Dermoscopy of a skin lesion: 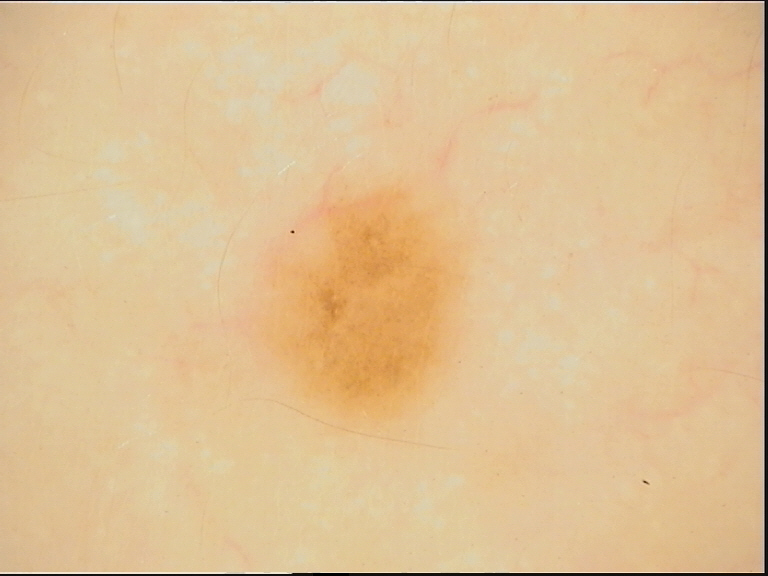Conclusion: The diagnostic label was a banal lesion — a junctional nevus.